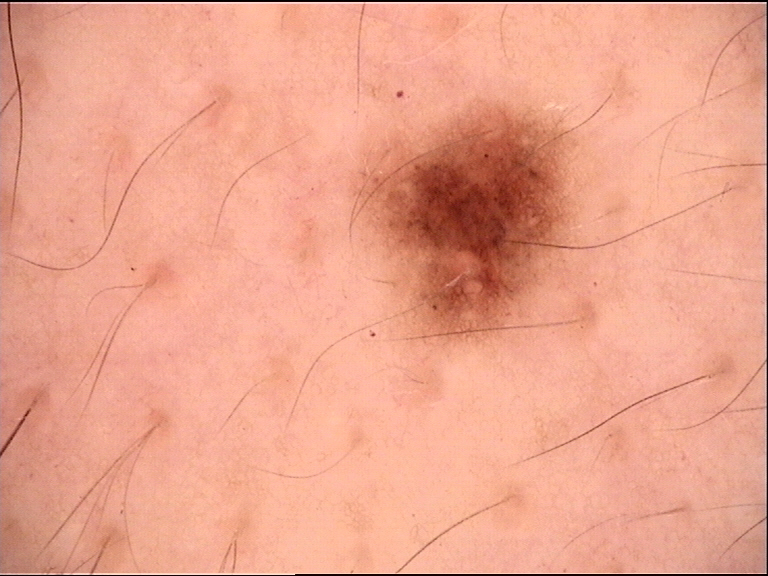* image: dermoscopy
* classification: banal
* diagnostic label: junctional nevus (expert consensus)